A clinical photograph of a skin lesion · a male patient about 30 years old.
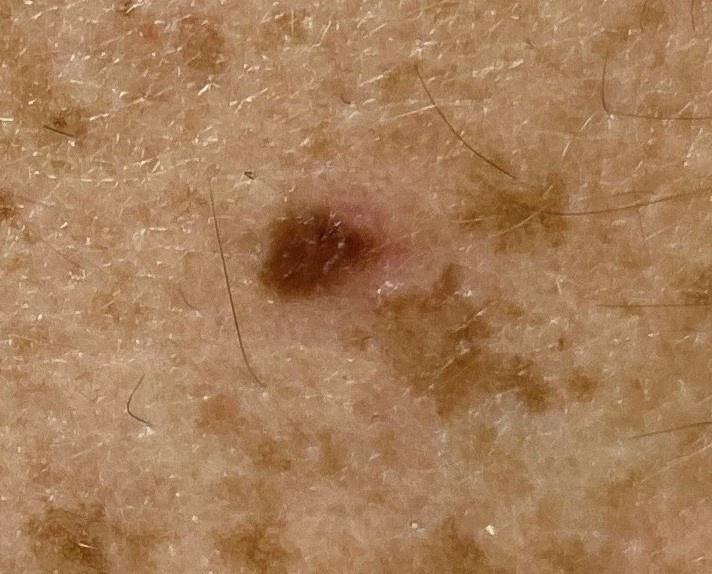The clinical impression was a benign lesion — a nevus.